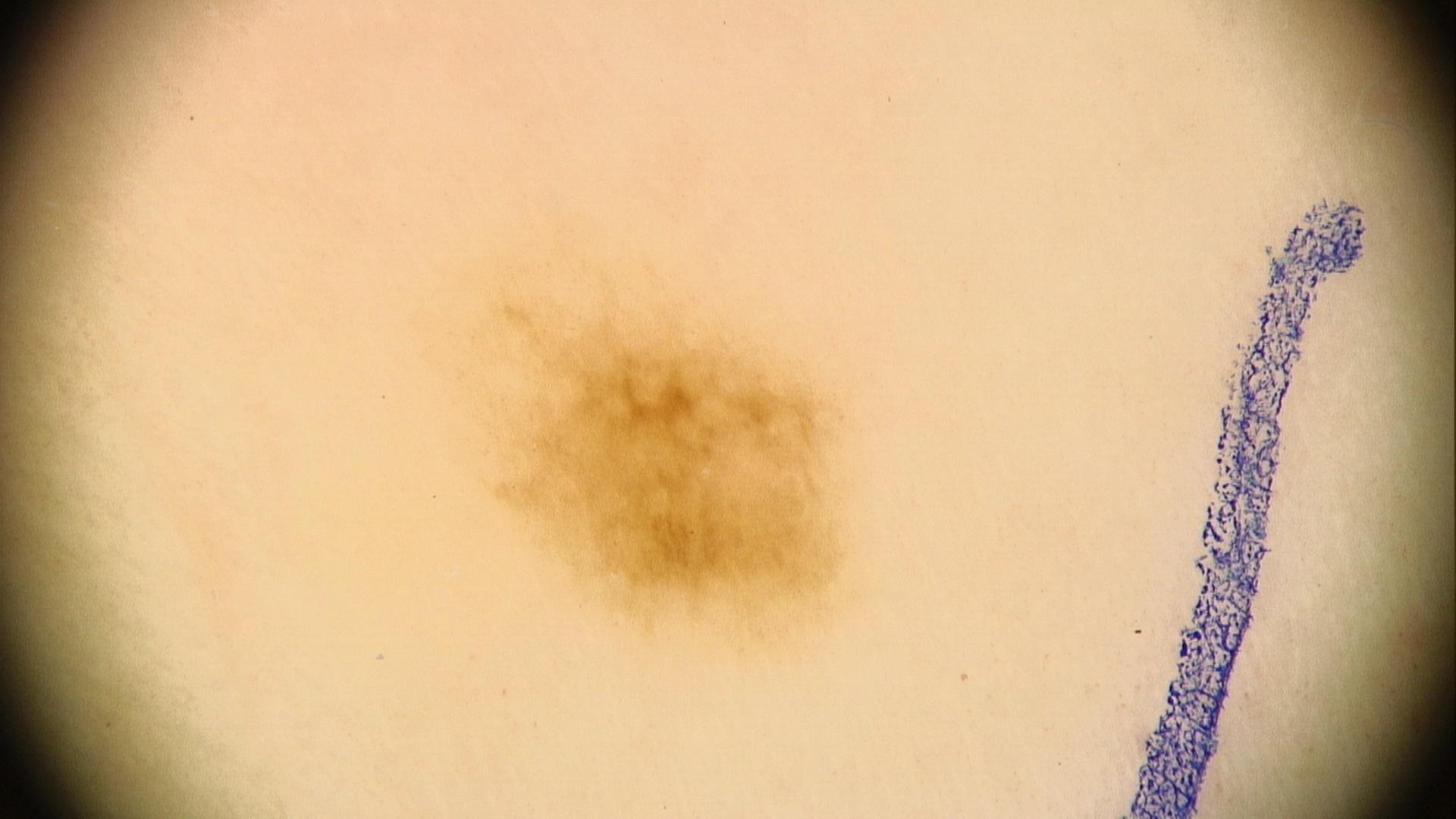Assessment: The clinical impression was a nevus.